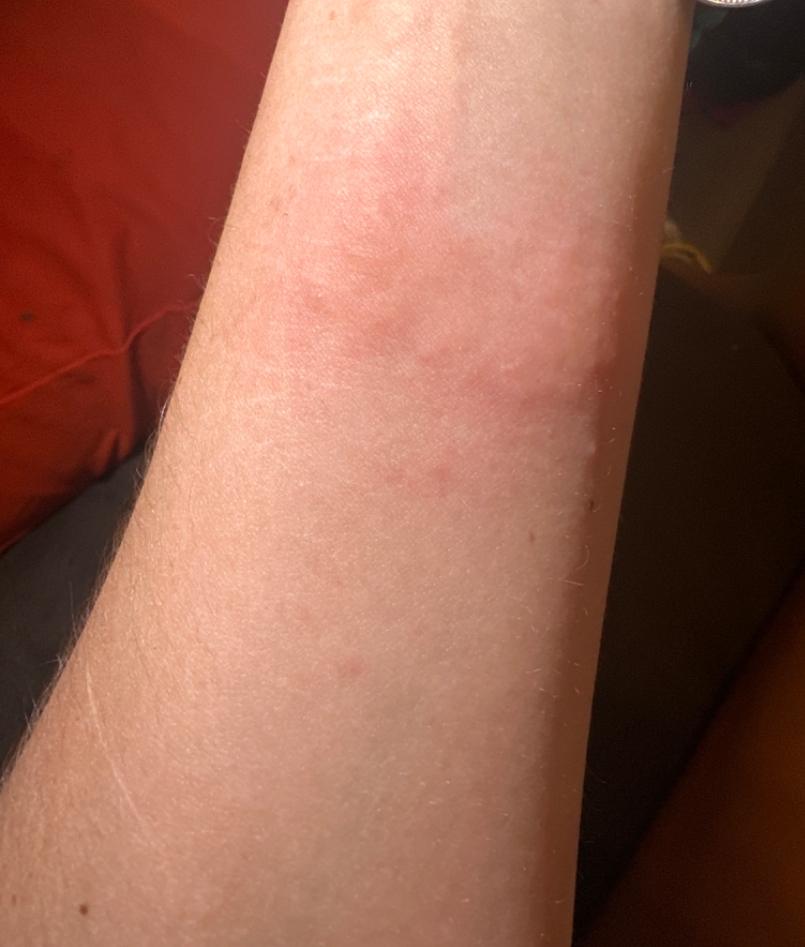assessment=unable to determine
skin tone=Fitzpatrick skin type III; lay reviewers estimated Monk skin tone scale 3 (US pool) or 2 (India pool)
present for=about one day
affected area=arm
subject=female, age 18–29
shot type=close-up
self-categorized as=a rash